A dermoscopic image of a skin lesion.
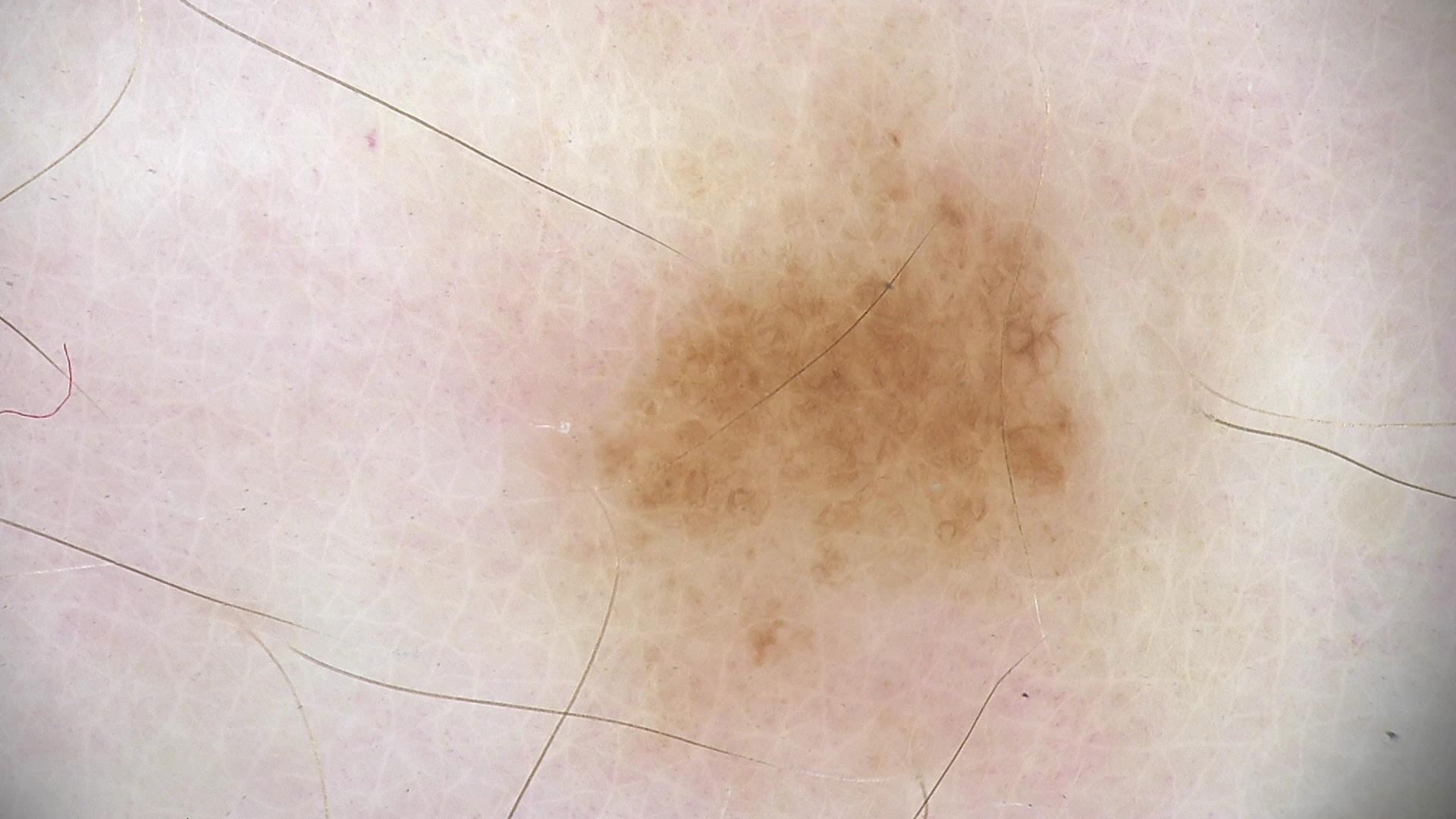Q: What is this lesion?
A: dysplastic junctional nevus (expert consensus)